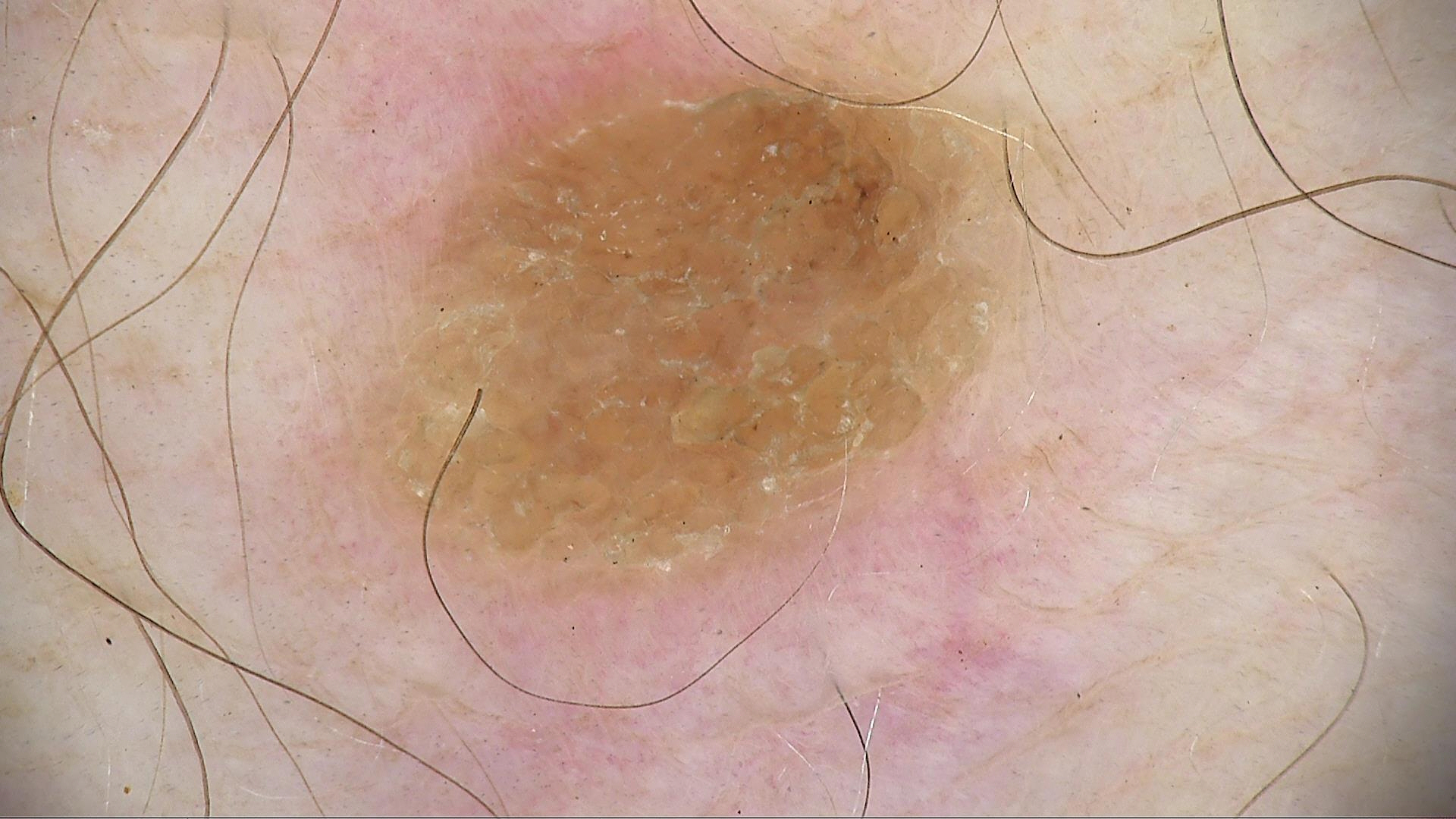modality = dermatoscopy; classification = keratinocytic; diagnosis = seborrheic keratosis (expert consensus).